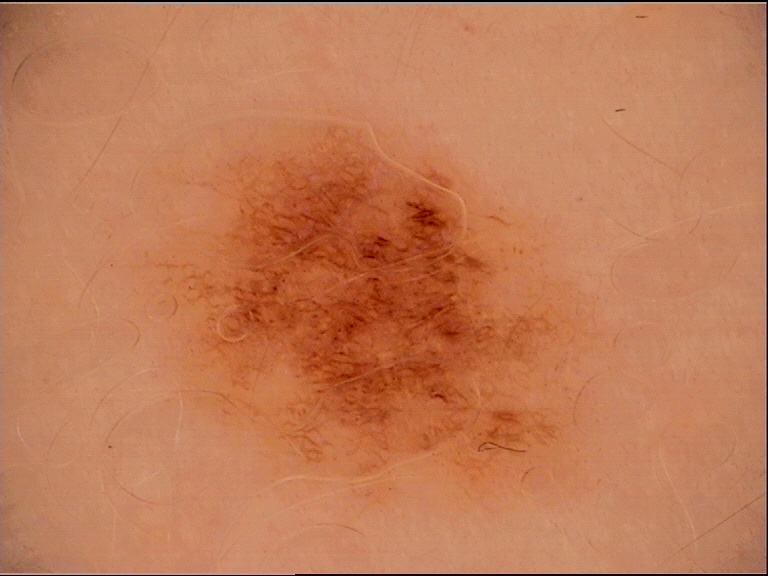diagnosis:
  name: dysplastic junctional nevus
  code: jd
  malignancy: benign
  super_class: melanocytic
  confirmation: expert consensus